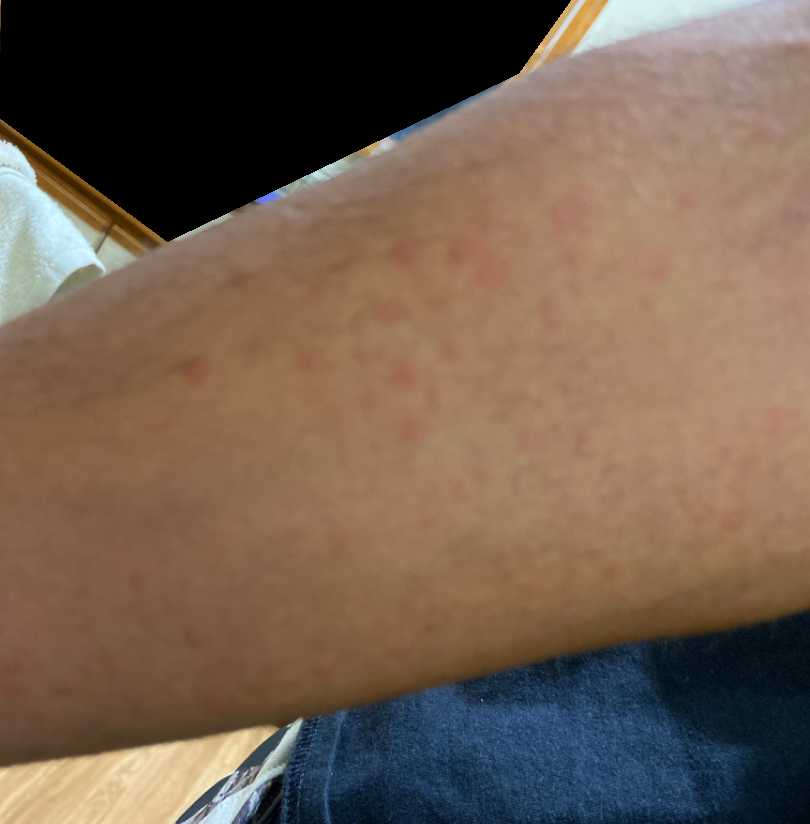assessment: could not be assessed | view: close-up | contributor: male, age 18–29 | location: leg, arm and head or neck.